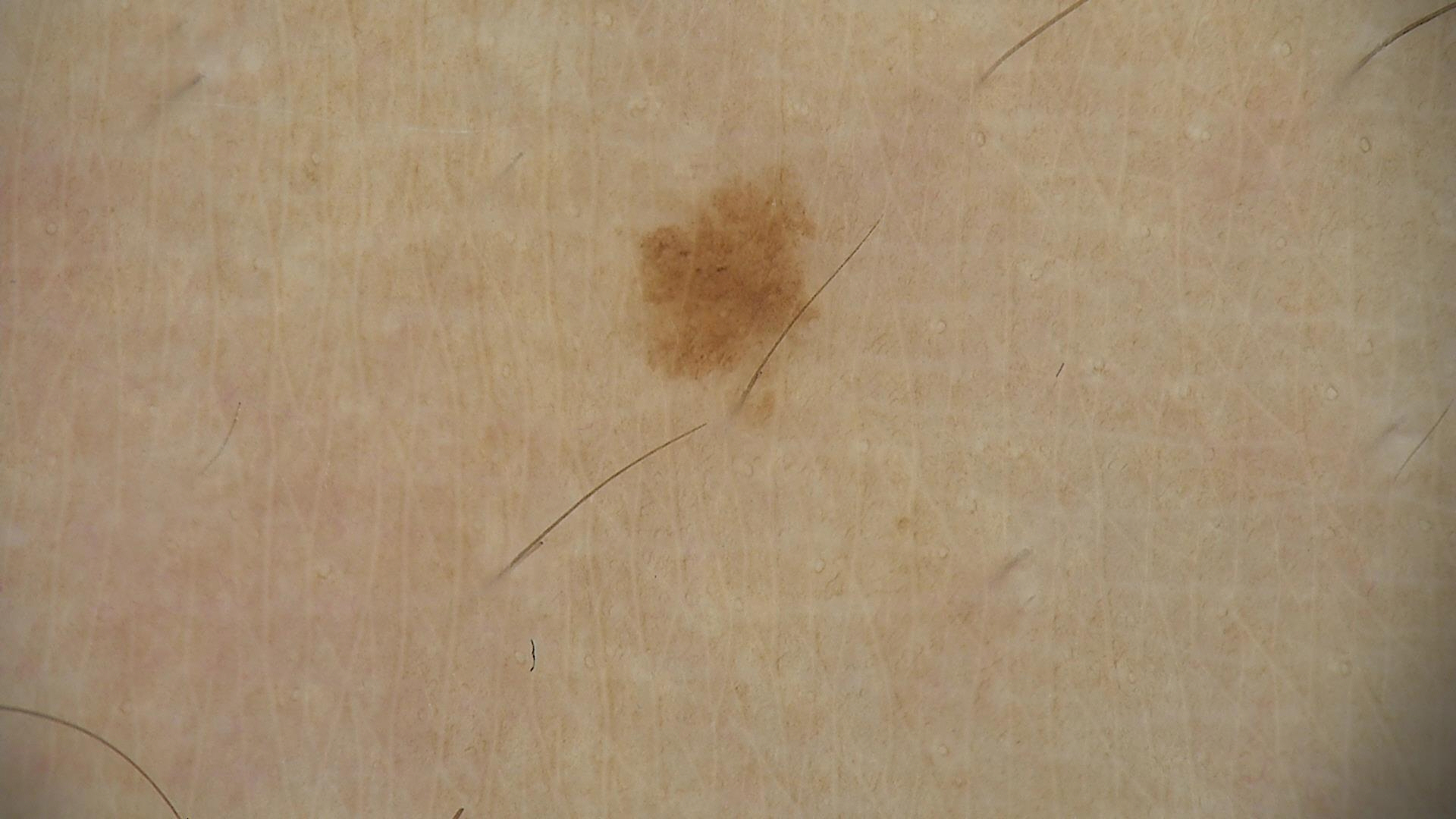Diagnosed as a dysplastic junctional nevus.